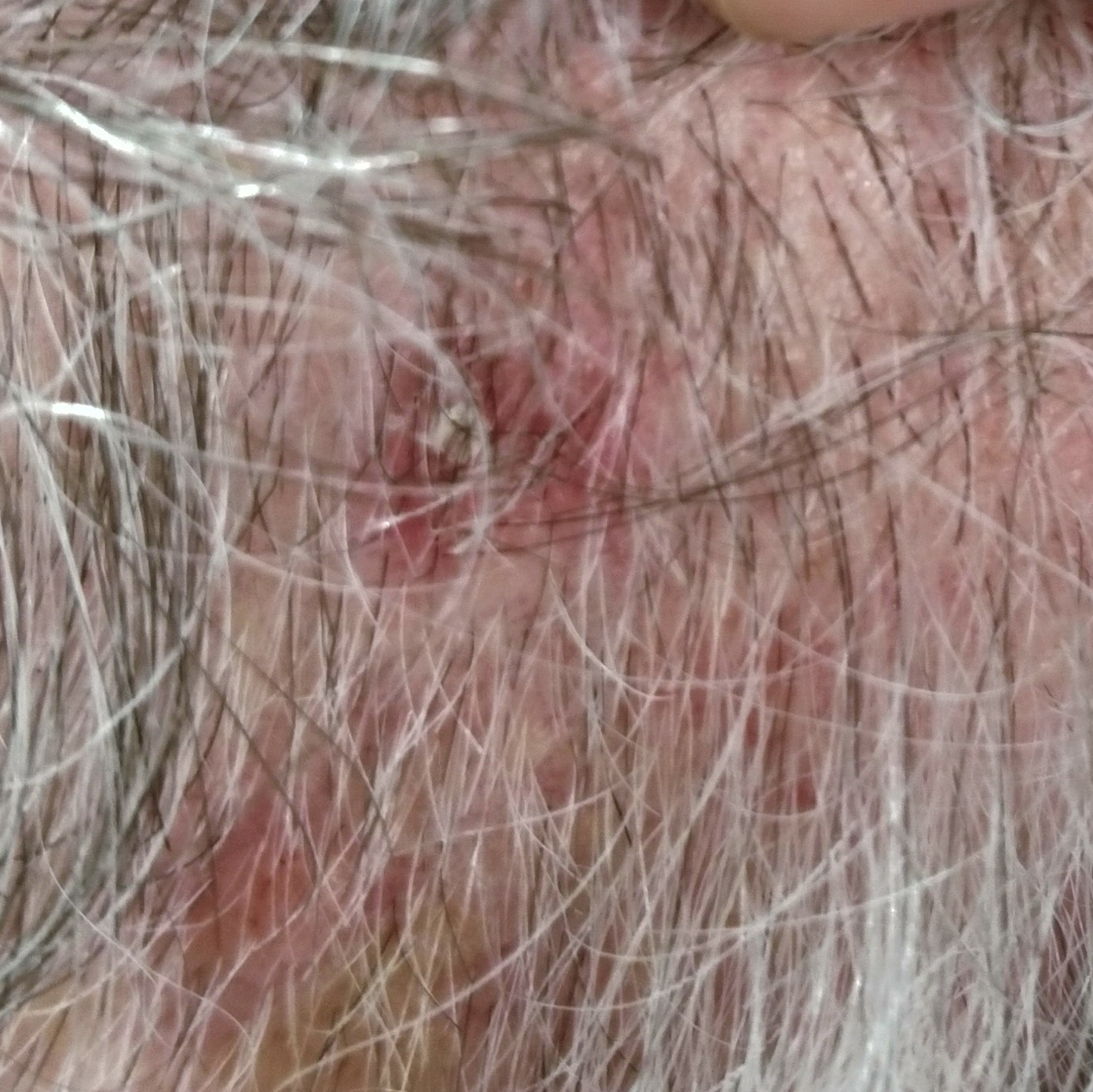Patient and lesion: A male subject 64 years of age. The chart notes prior malignancy (patient or family) and alcohol use. Fitzpatrick II. A clinical photograph of a skin lesion. The lesion is on the face. Measuring about 12 × 10 mm. Conclusion: The biopsy diagnosis was a lesion with uncertain malignant potential — an actinic keratosis.